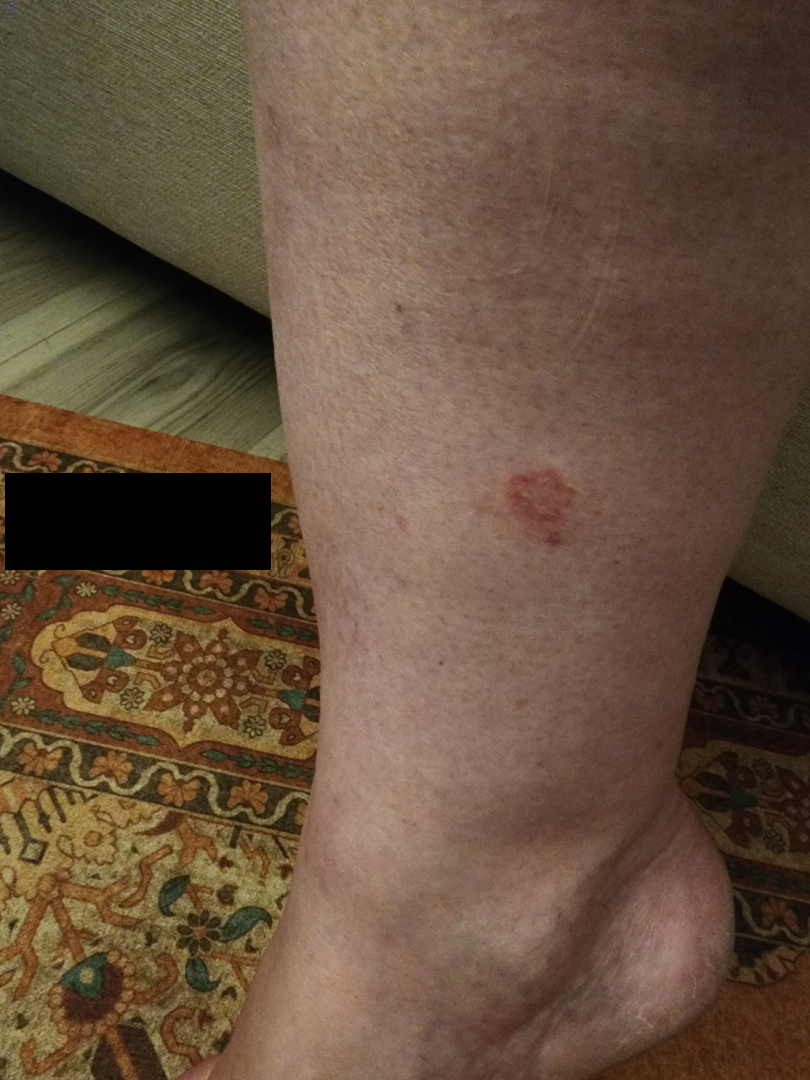• dermatologist impression: Tinea (possible); Eczema (possible); Pityriasis rosea (lower probability)